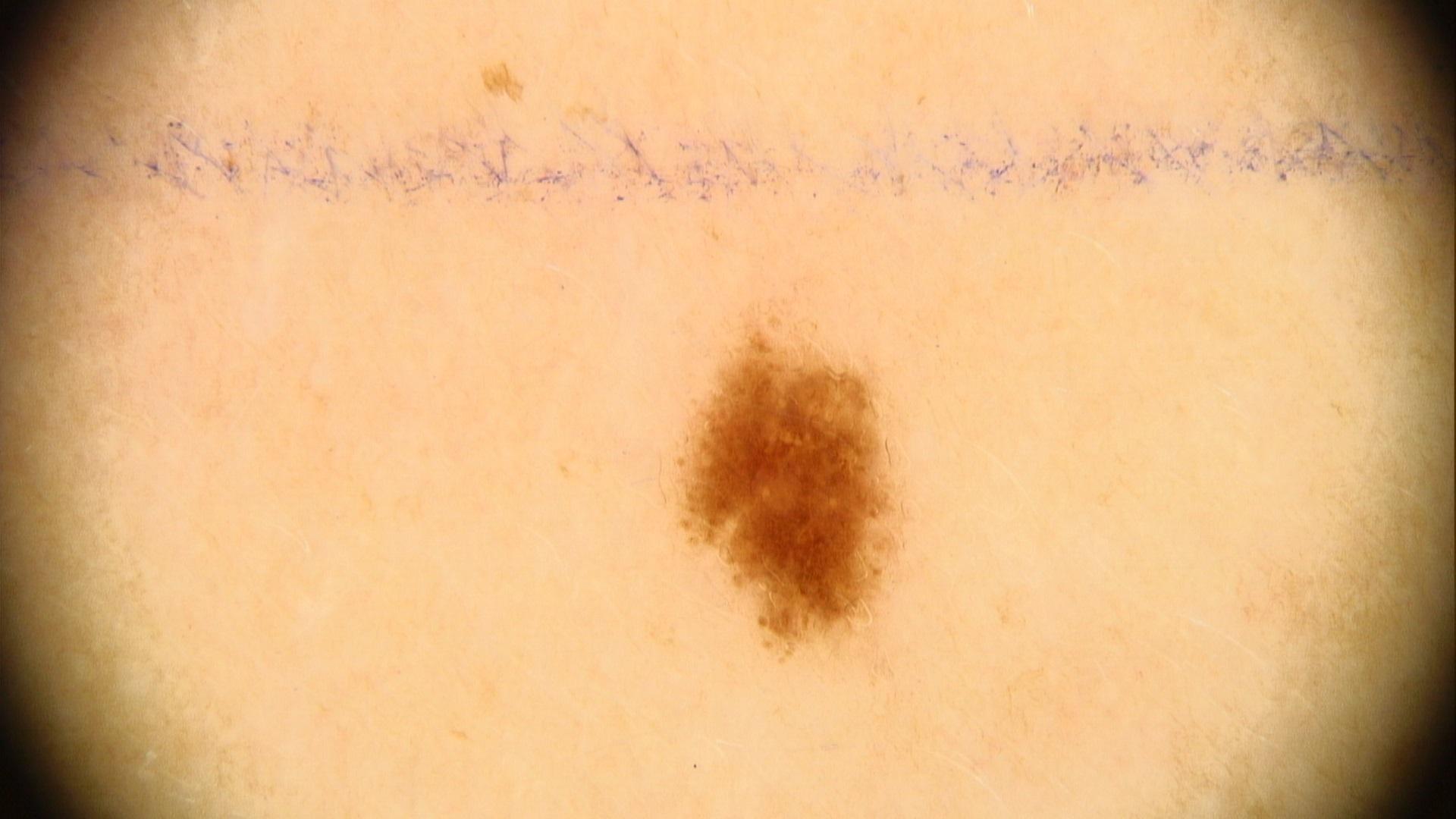| field | value |
|---|---|
| modality | dermoscopy |
| relevant background | a first-degree relative with melanoma |
| subject | male, roughly 40 years of age |
| location | the trunk |
| assessment | Nevus |